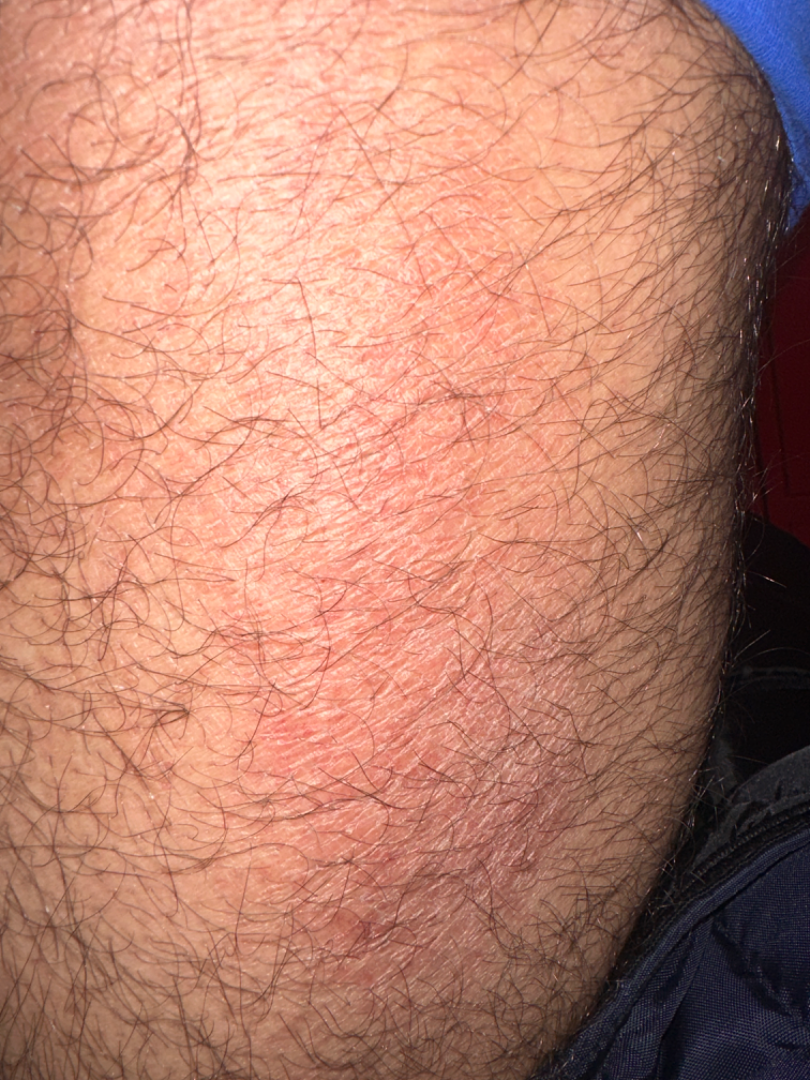- self-categorized as · a rash
- symptoms · enlargement, bleeding and itching
- described texture · rough or flaky
- body site · arm and leg
- contributor · male, age 18–29
- duration · one to three months
- image framing · at an angle
- skin tone · Fitzpatrick skin type II; lay reviewers estimated Monk skin tone scale 3–4
- assessment · the leading consideration is Acute and chronic dermatitis; an alternative is Xerosis; also consider Eczema; possibly Irritant Contact Dermatitis